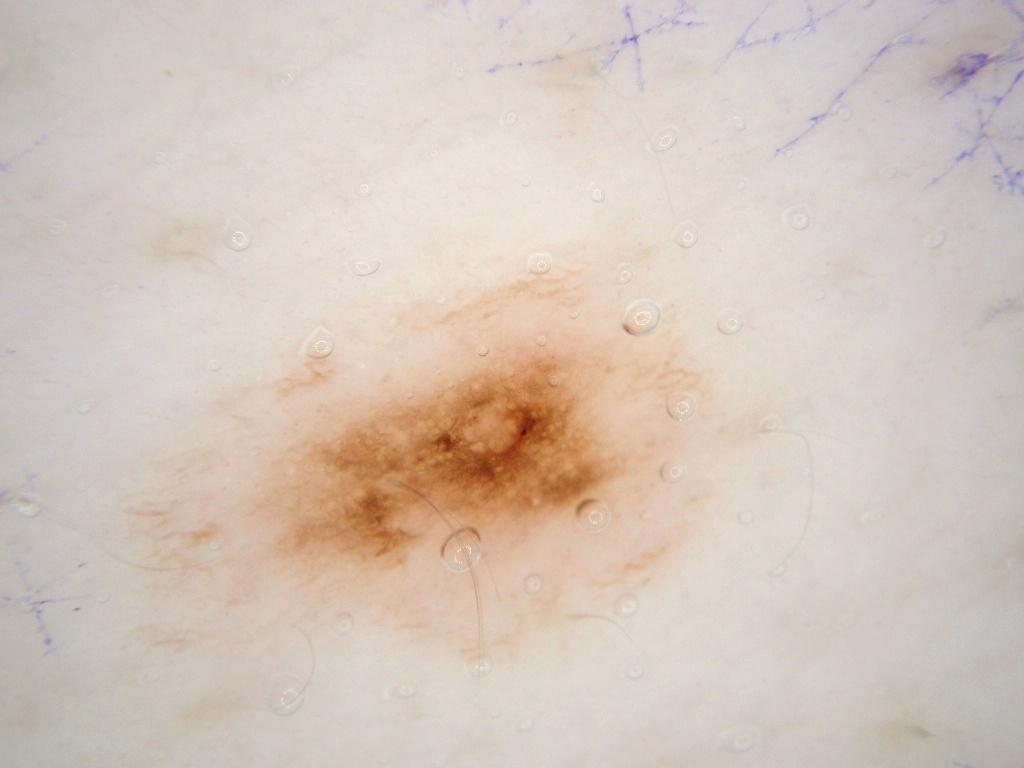imaging — dermoscopy
size — moderate
location — left=120, top=225, right=758, bottom=683
features — pigment network; absent: globules, milia-like cysts, streaks, and negative network
assessment — a melanocytic nevus, a benign lesion